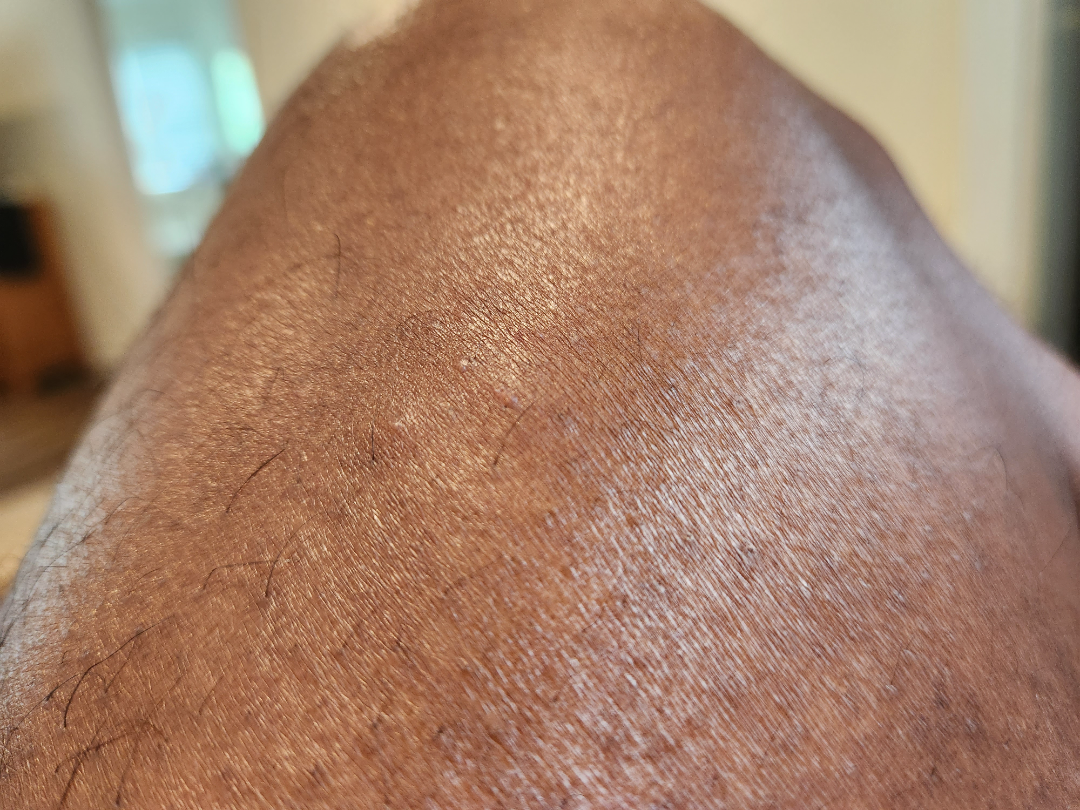Case summary:
- body site · leg
- contributor · male
- image framing · at an angle
- present for · about one day
- symptoms · itching
- skin tone · lay reviewers estimated Monk skin tone scale 4 or 6 (two reviewer pools disagreed)
- patient's own categorization · a rash
- dermatologist impression · Eczema (most likely); Scabies (remote); Folliculitis (remote); Tinea (remote); Irritant Contact Dermatitis (remote)